A patient 80 years old · a clinical photo of a skin lesion taken with a smartphone: 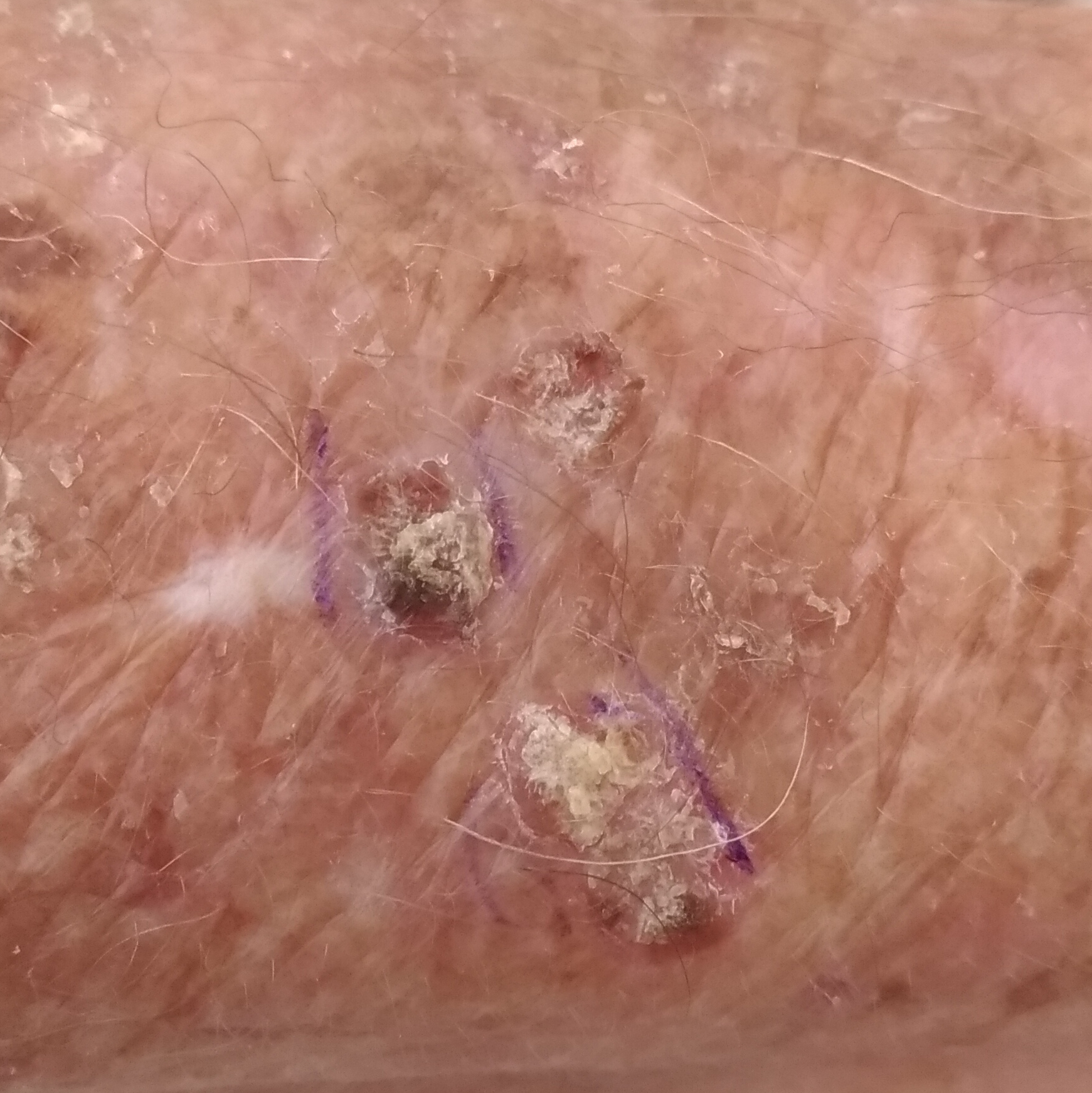<skin_lesion>
  <lesion_location>a forearm</lesion_location>
  <diagnosis>
    <name>actinic keratosis</name>
    <code>ACK</code>
    <malignancy>indeterminate</malignancy>
    <confirmation>clinical consensus</confirmation>
  </diagnosis>
</skin_lesion>